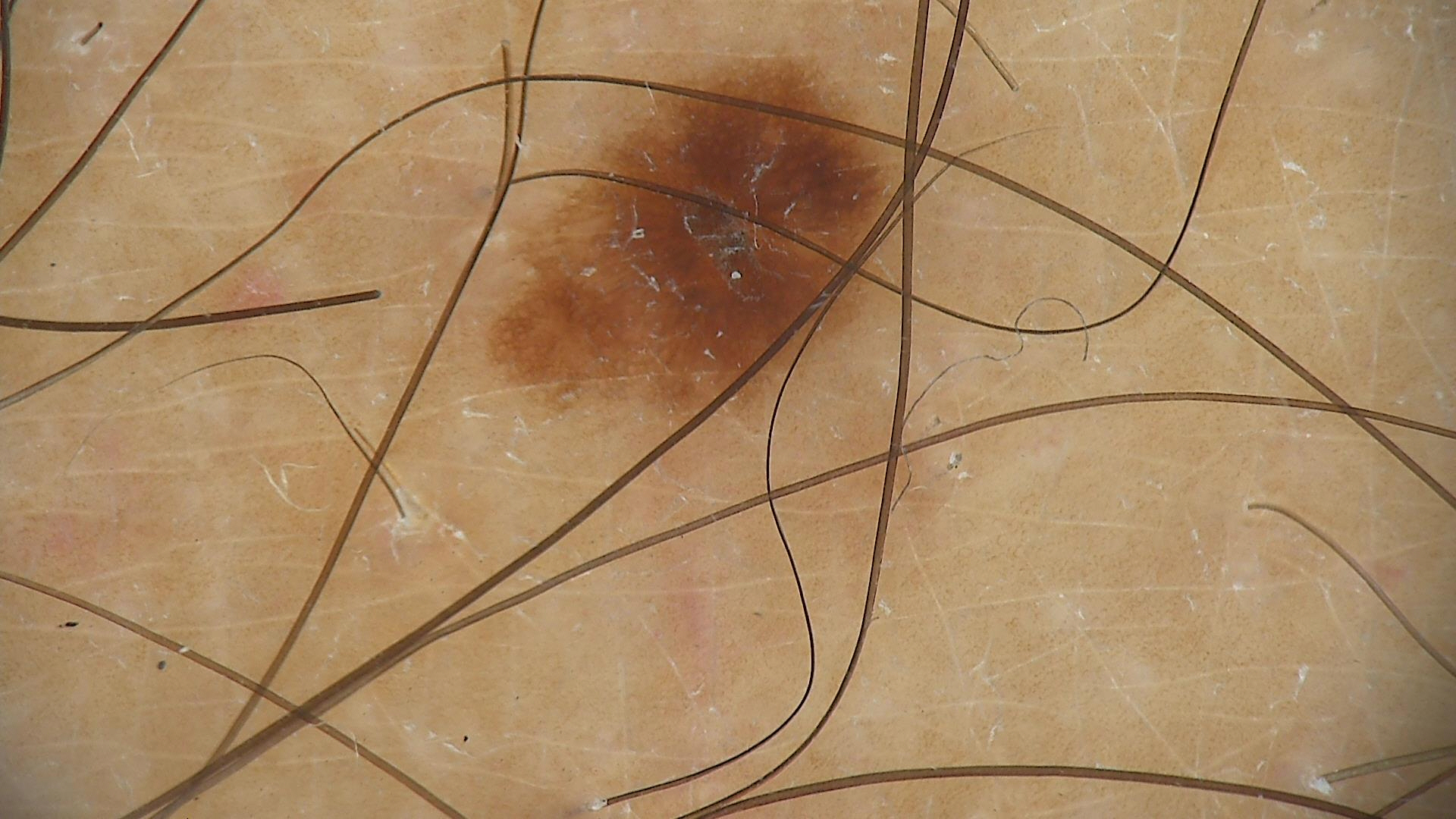{
  "image": "dermoscopy",
  "diagnosis": {
    "name": "dysplastic junctional nevus",
    "code": "jd",
    "malignancy": "benign",
    "super_class": "melanocytic",
    "confirmation": "expert consensus"
  }
}